A skin lesion imaged with a dermatoscope: 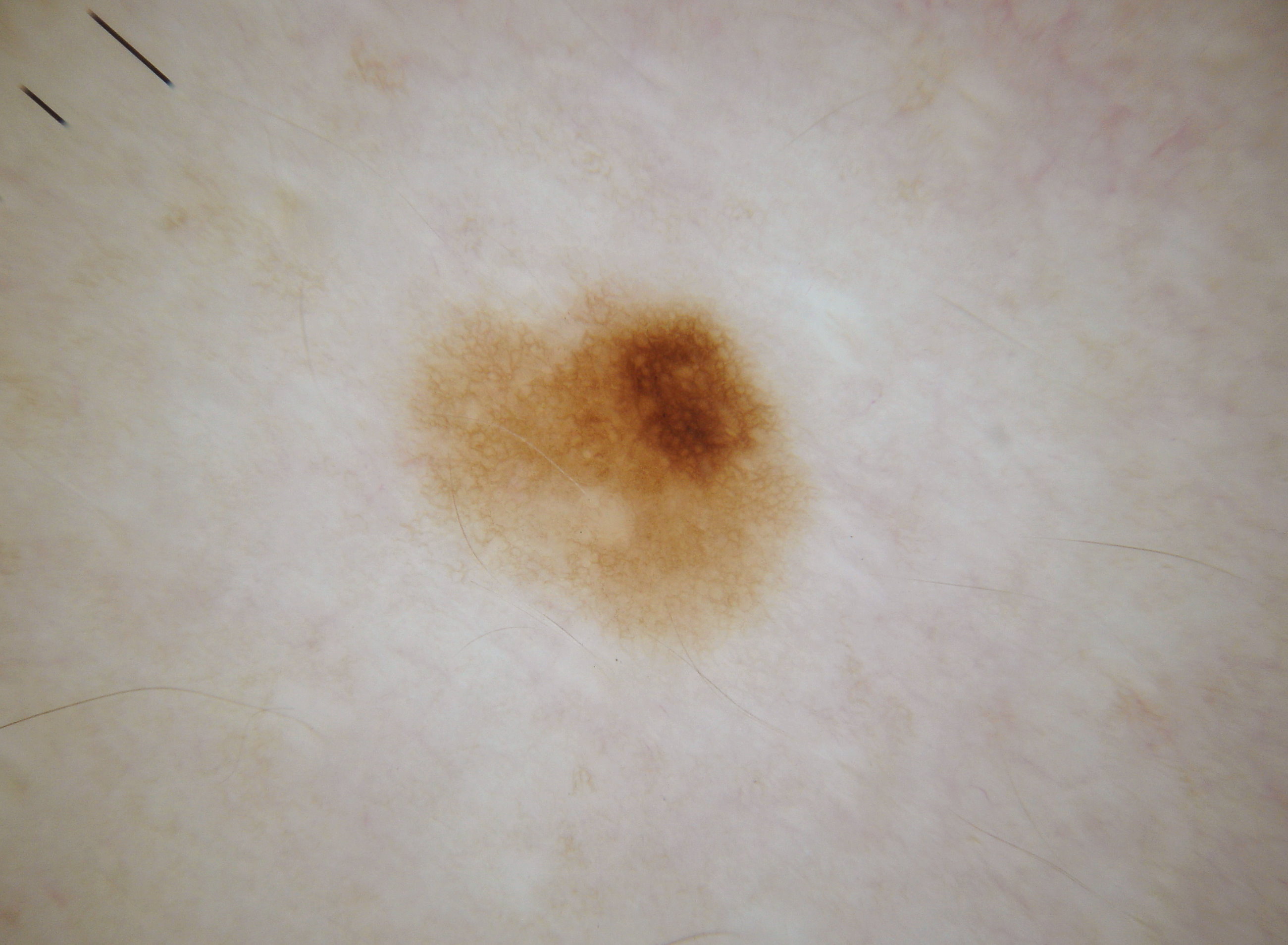On dermoscopy, the lesion shows pigment network; no milia-like cysts, streaks, globules, or negative network.
With coordinates (x1, y1, x2, y2), lesion location: <bbox>400, 277, 814, 649</bbox>.
The lesion takes up a moderate portion of the field.
Consistent with a melanocytic nevus, a benign skin lesion.